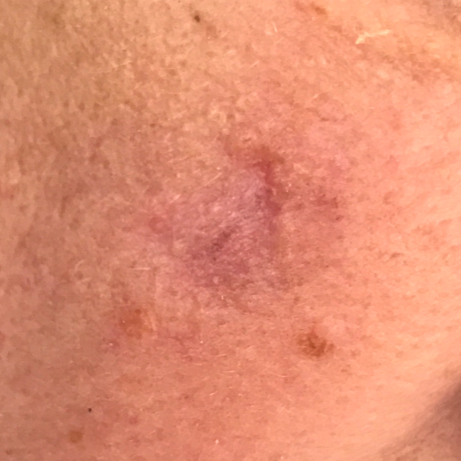The patient was assessed as skin type III. History notes prior malignancy (patient or family) and prior skin cancer (patient or family). A female subject 55 years of age. A clinical photograph of a skin lesion. The lesion was found on the face. The lesion measures 10 × 4 mm. By the patient's account, the lesion has grown, is elevated, and has changed. Biopsy-confirmed as a basal cell carcinoma.